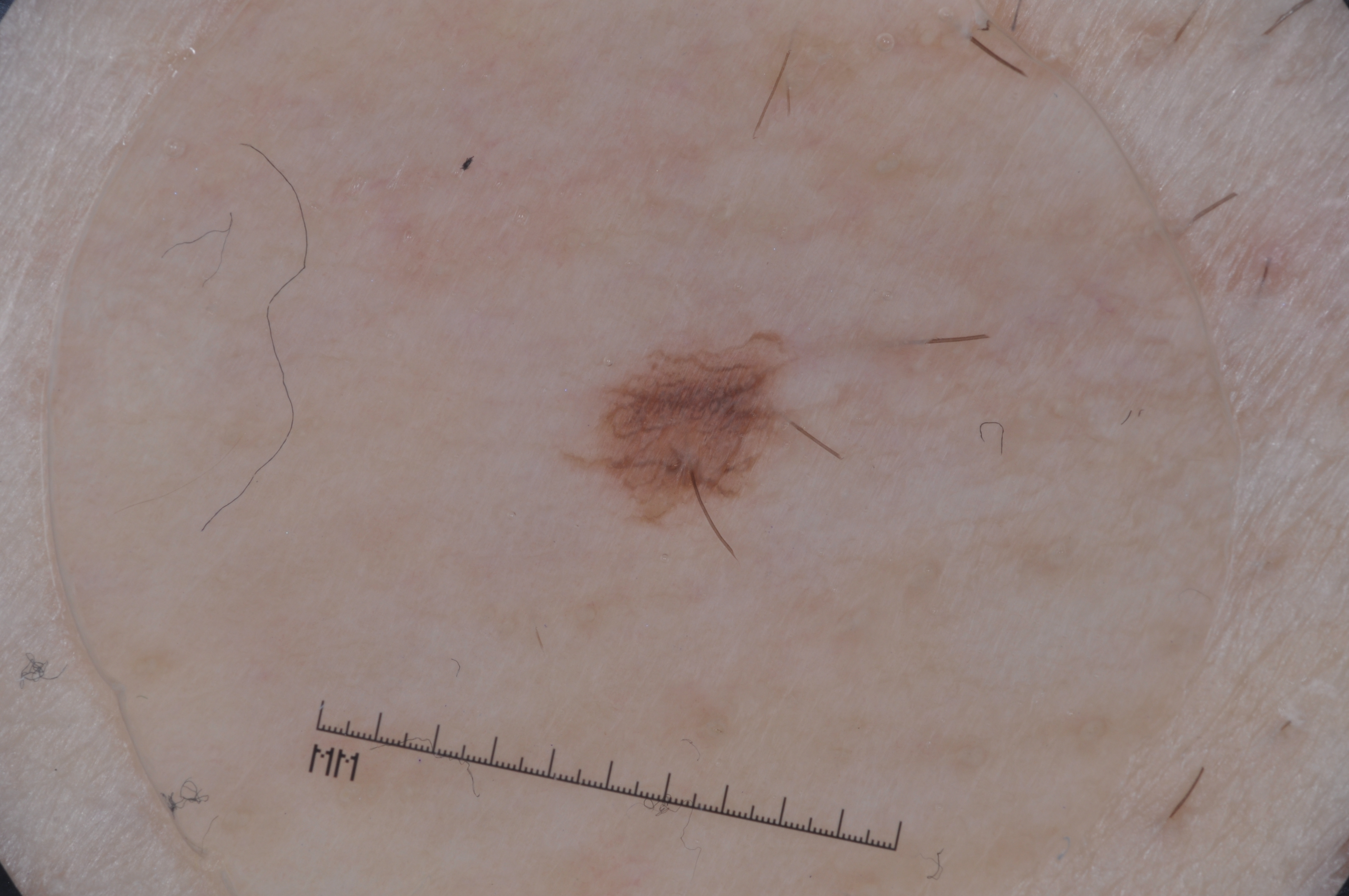{"image": {"modality": "dermoscopy"}, "patient": {"sex": "female", "age_approx": 60}, "lesion_extent": {"approx_field_fraction_pct": 3}, "lesion_location": {"bbox_xyxy": [559, 311, 844, 561]}, "dermoscopic_features": {"present": [], "absent": ["negative network", "streaks", "milia-like cysts", "pigment network"]}, "diagnosis": {"name": "melanocytic nevus", "malignancy": "benign", "lineage": "melanocytic", "provenance": "clinical"}}